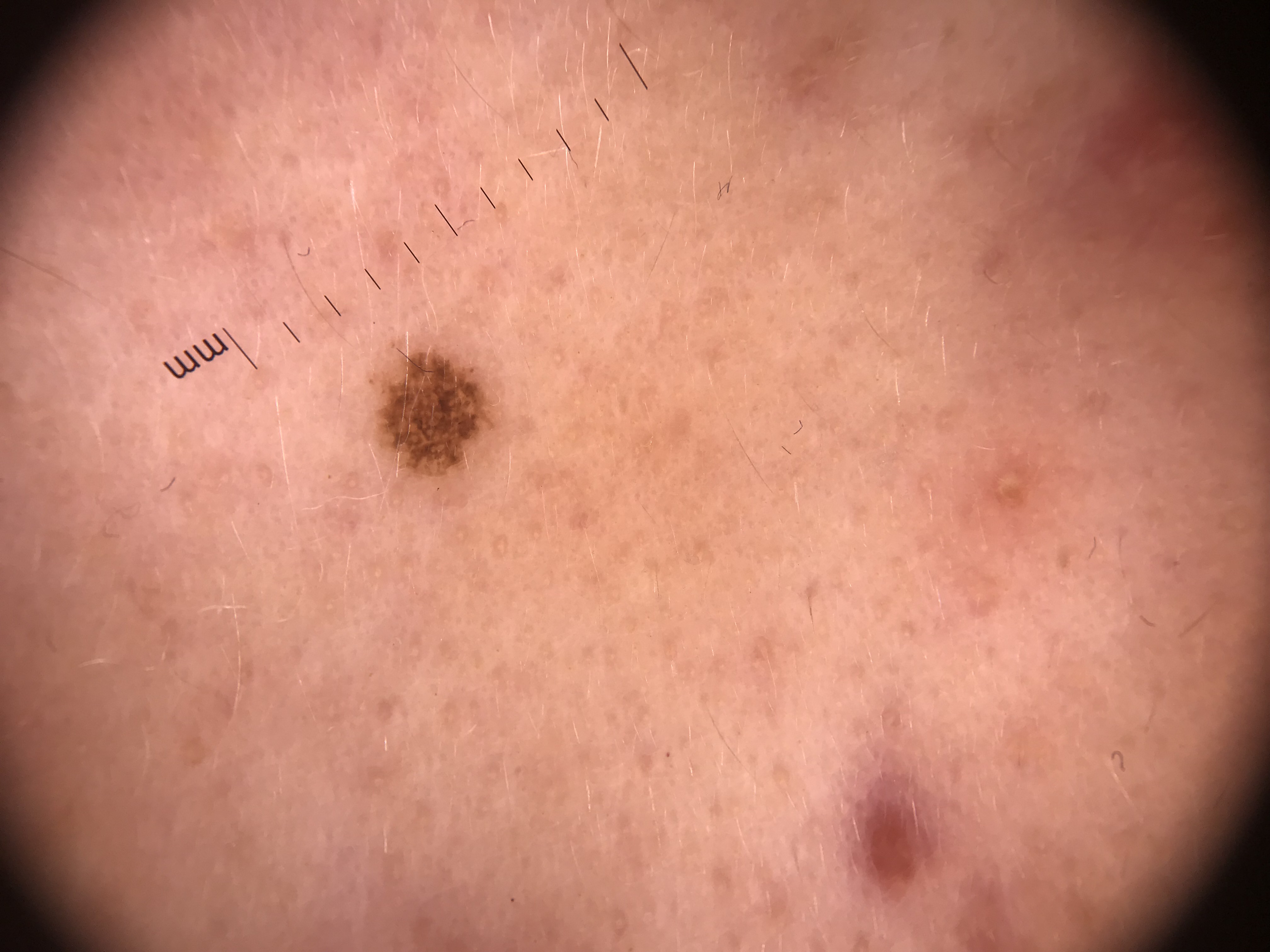<dermoscopy>
<image>dermatoscopy</image>
<diagnosis>
<name>dysplastic junctional nevus</name>
<code>jd</code>
<malignancy>benign</malignancy>
<super_class>melanocytic</super_class>
<confirmation>expert consensus</confirmation>
</diagnosis>
</dermoscopy>